A dermoscopic photograph of a skin lesion: 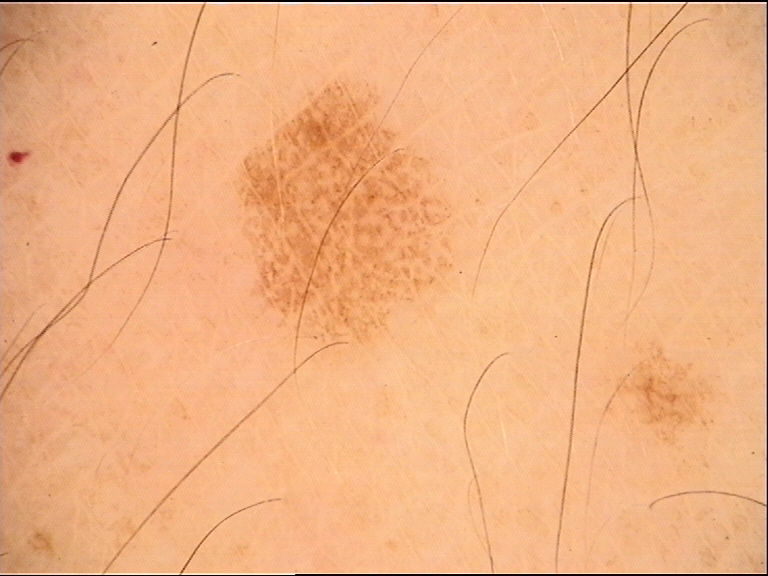Labeled as a dysplastic junctional nevus.